An image taken at an angle, FST II; lay reviewers estimated Monk Skin Tone 3 (US pool) or 2 (India pool).
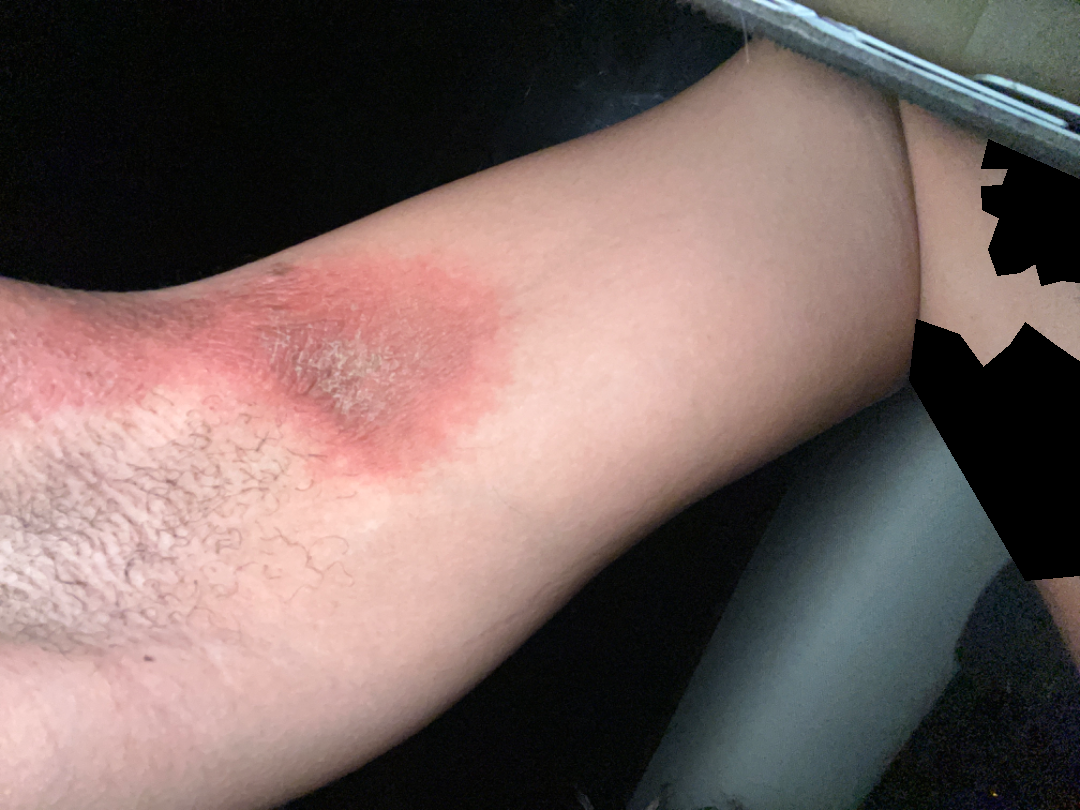Notes:
– assessment · not assessable